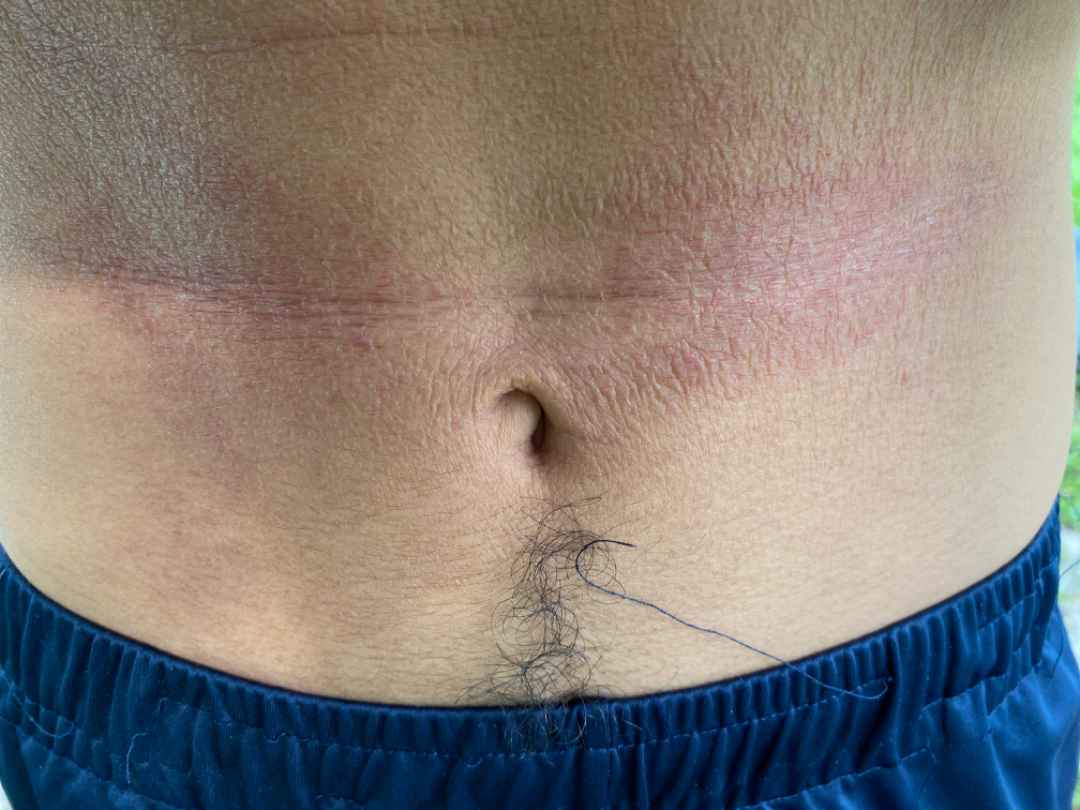Clinical context: Self-categorized by the patient as skin that appeared healthy to them. Close-up view. No relevant systemic symptoms. The patient is male. Skin tone: Fitzpatrick phototype IV; lay reviewers estimated Monk Skin Tone 2 (US pool) or 3 (India pool). Texture is reported as rough or flaky. Located on the front of the torso. Assessment: Allergic Contact Dermatitis (most likely); Irritant Contact Dermatitis (considered).